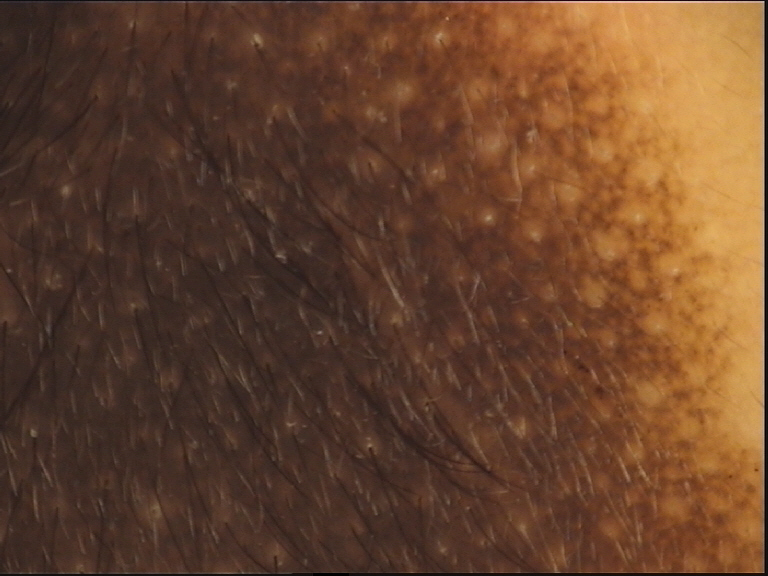{
  "diagnosis": {
    "name": "congenital compound nevus",
    "code": "ccb",
    "malignancy": "benign",
    "super_class": "melanocytic",
    "confirmation": "expert consensus"
  }
}